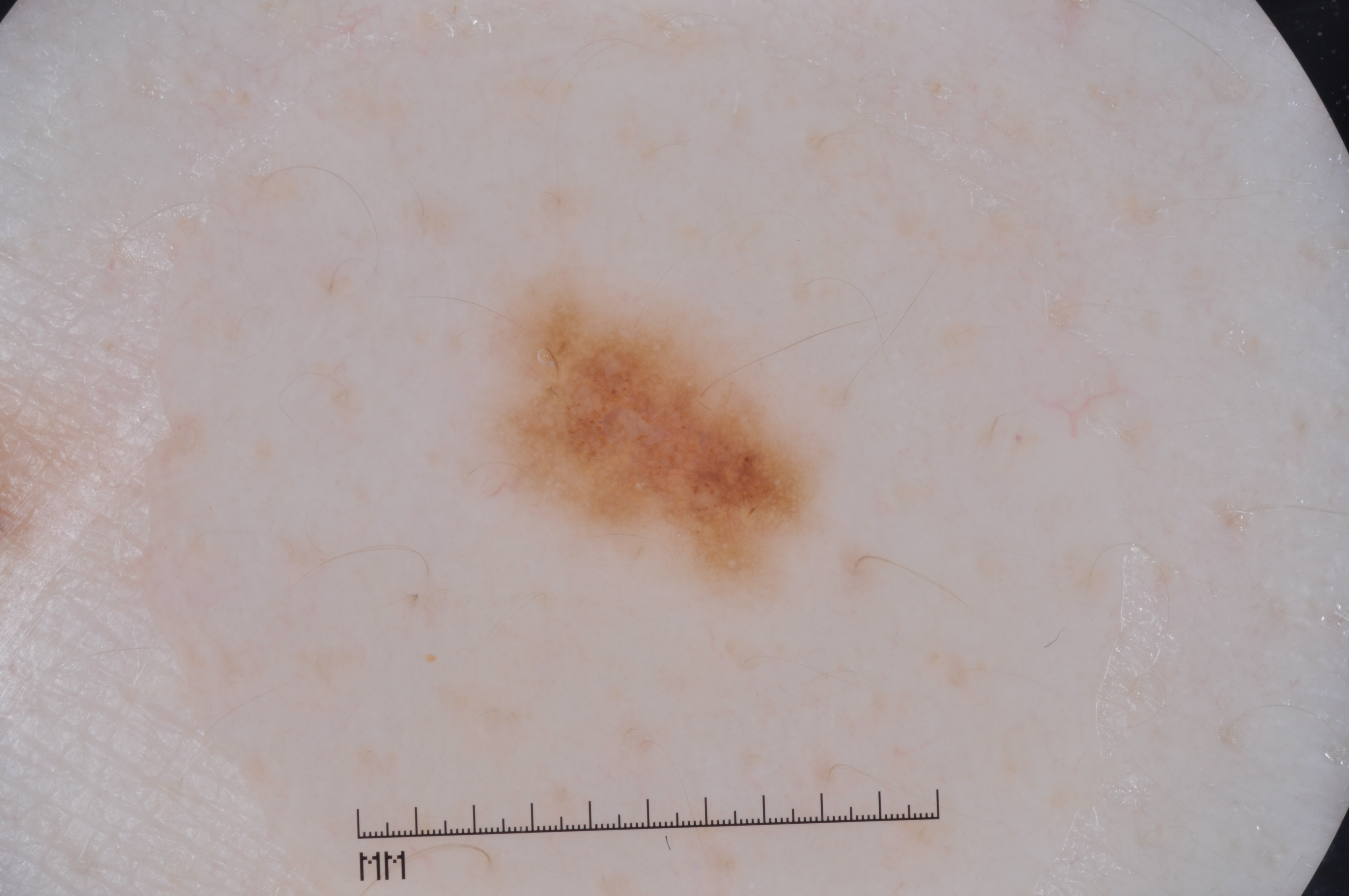Image and clinical context:
Dermoscopy of a skin lesion. A female subject approximately 50 years of age. Dermoscopic assessment notes pigment network and milia-like cysts, with no negative network or streaks. With coordinates (x1, y1, x2, y2), the lesion's extent is bbox=[486, 274, 820, 595].
Assessment:
Clinically diagnosed as a melanocytic nevus.